The photograph was taken at a distance · the arm is involved: 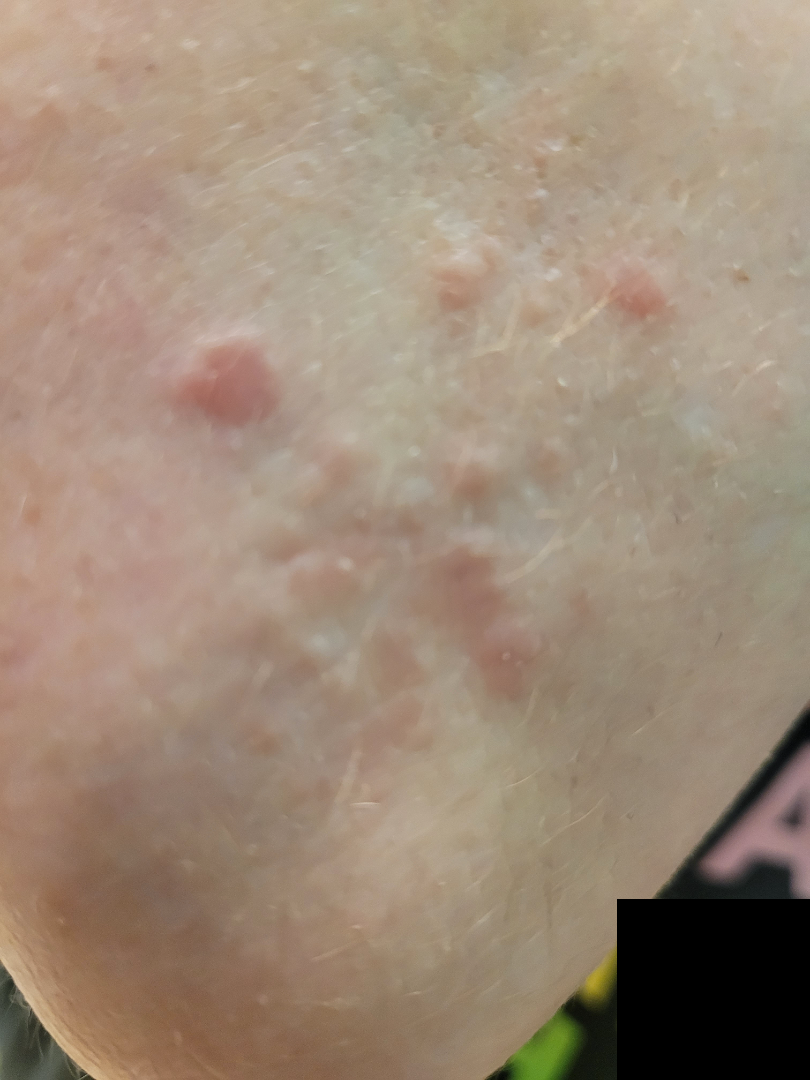Impression: The case was difficult to assess from the available photograph.